The photo was captured at a distance. Located on the leg and arm. The patient is a female aged 40–49 — 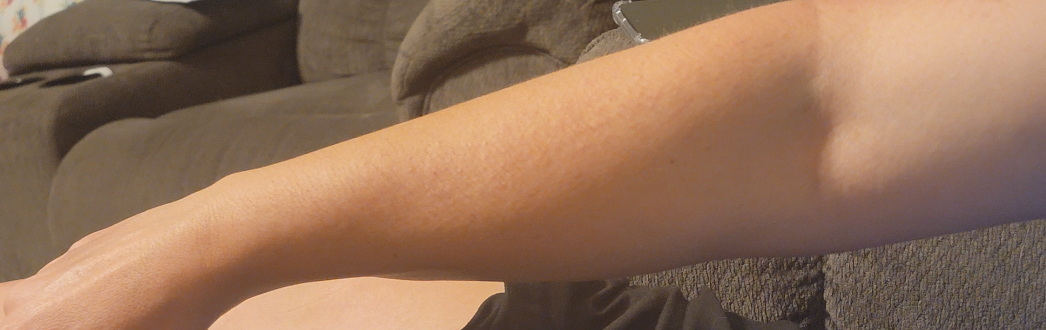Findings: The reviewer was unable to grade this case for skin condition.